This is a dermoscopic photograph of a skin lesion:
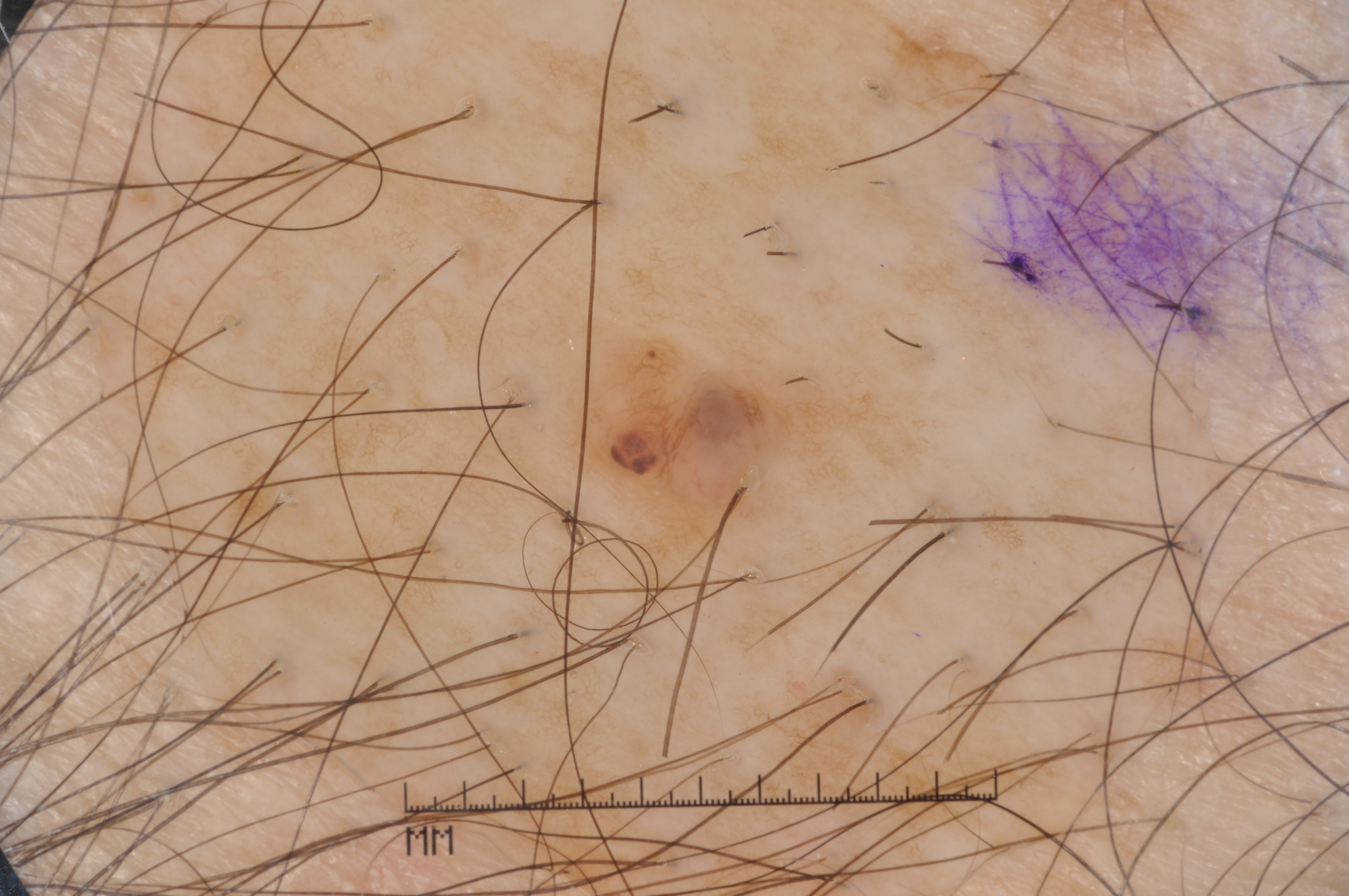{"lesion_extent": "small", "dermoscopic_features": {"present": ["pigment network"], "absent": ["negative network", "milia-like cysts", "streaks"]}, "lesion_location": {"bbox_xyxy": [561, 324, 815, 528]}, "diagnosis": {"name": "melanocytic nevus", "malignancy": "benign", "lineage": "melanocytic", "provenance": "clinical"}}